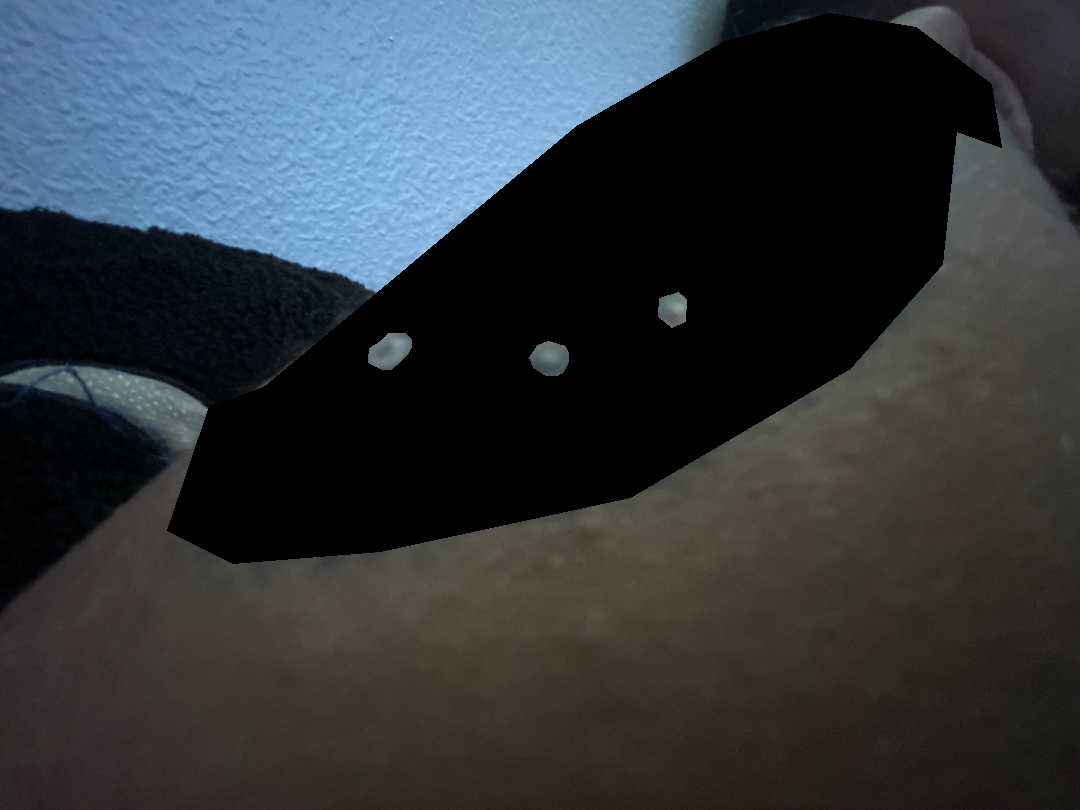<dermatology_case>
<assessment>ungradable on photographic review</assessment>
</dermatology_case>